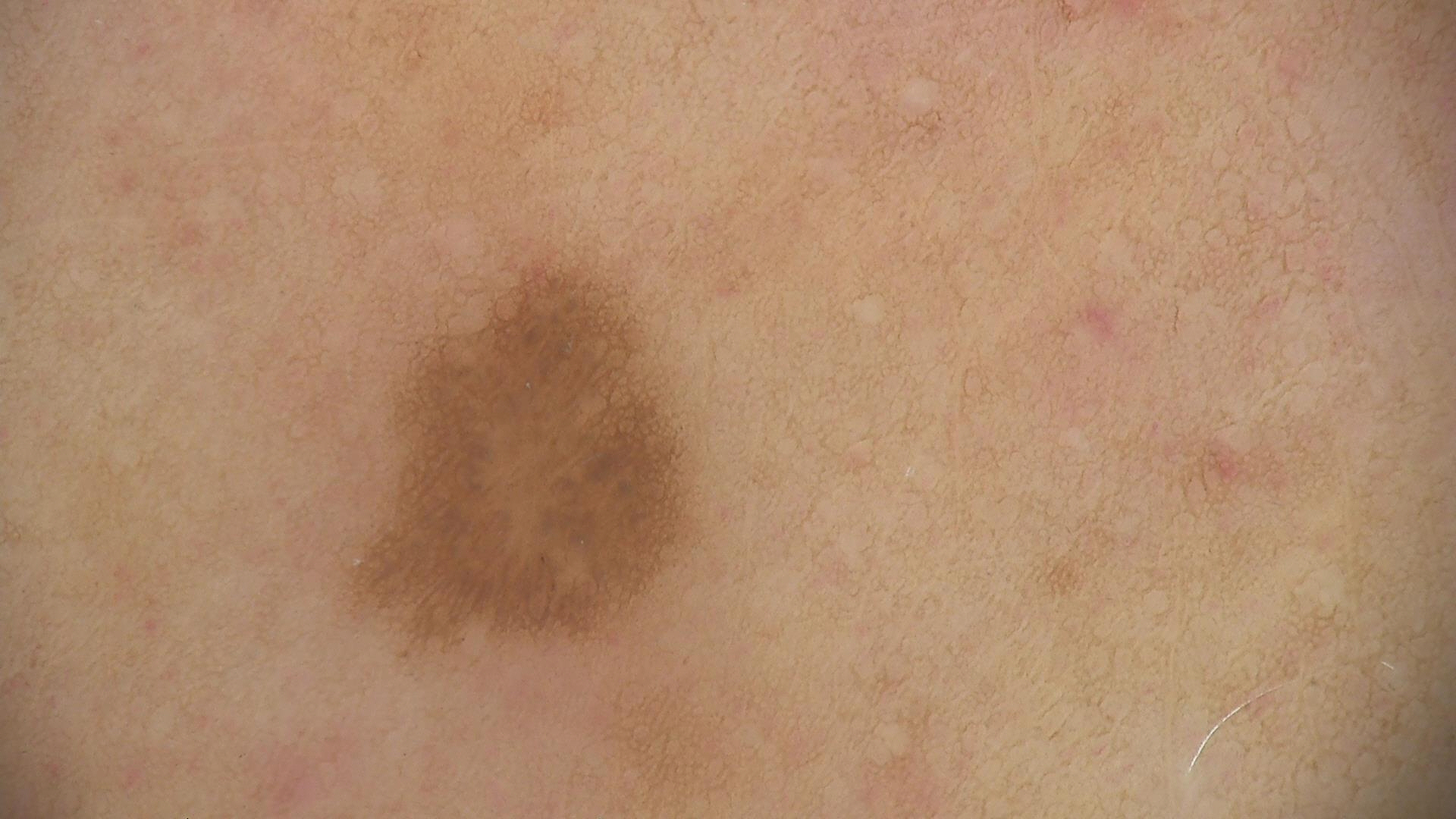Summary: A dermatoscopic image of a skin lesion. Conclusion: Classified as a benign lesion — a dysplastic junctional nevus.